Dermoscopy of a skin lesion.
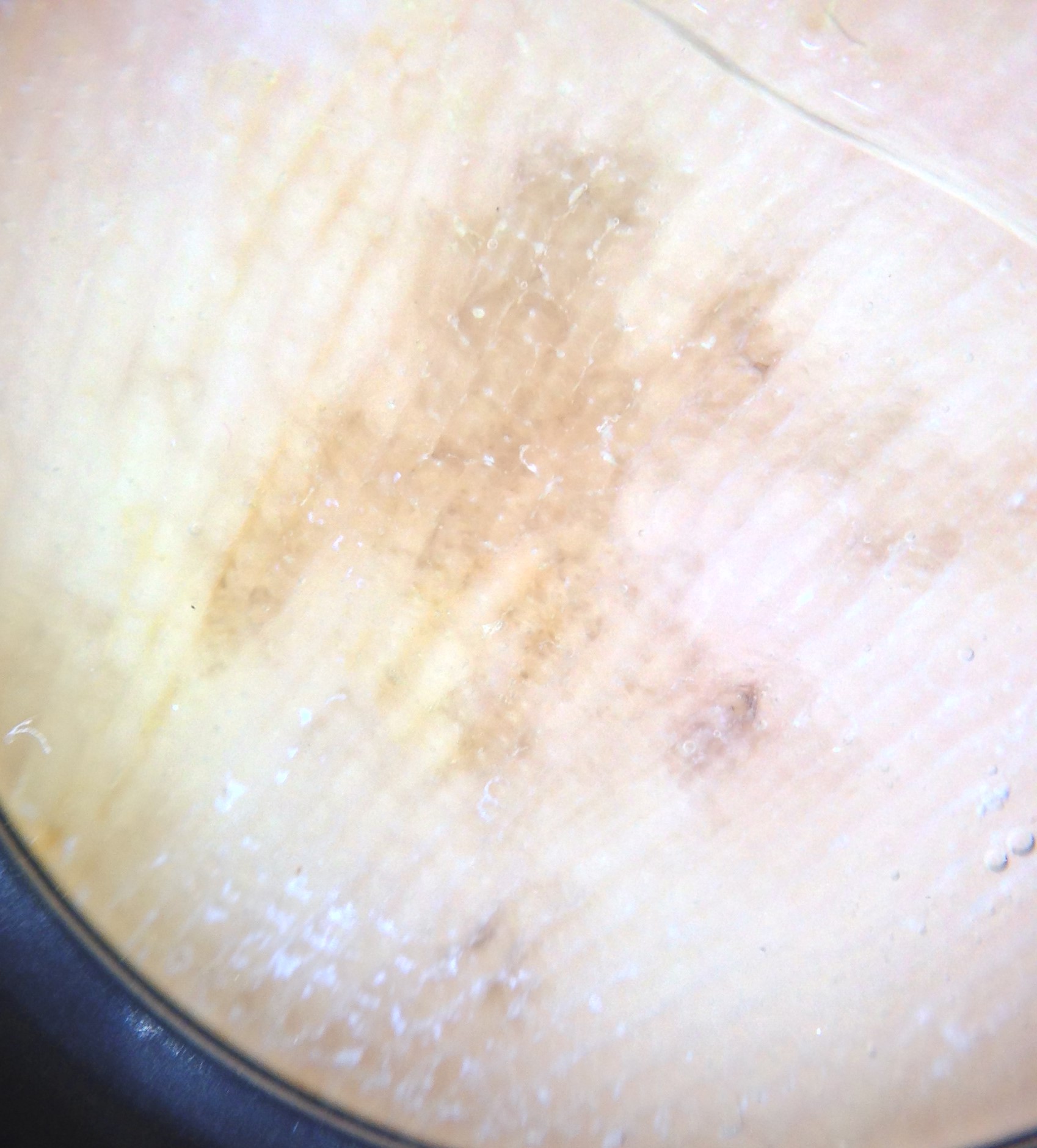label = acral lentiginous melanoma (biopsy-proven)